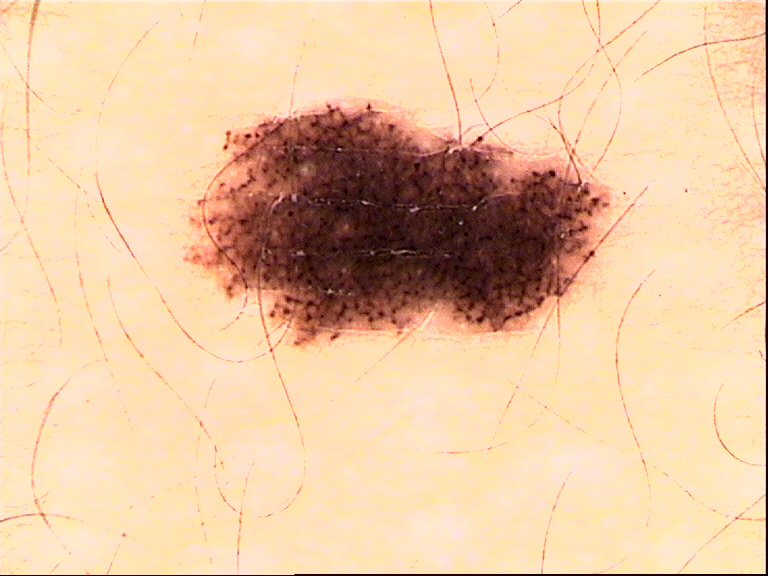A dermoscopic image of a skin lesion.
The diagnostic label was a dysplastic junctional nevus.